A male patient about 65 years old · the chart notes a previous melanoma.
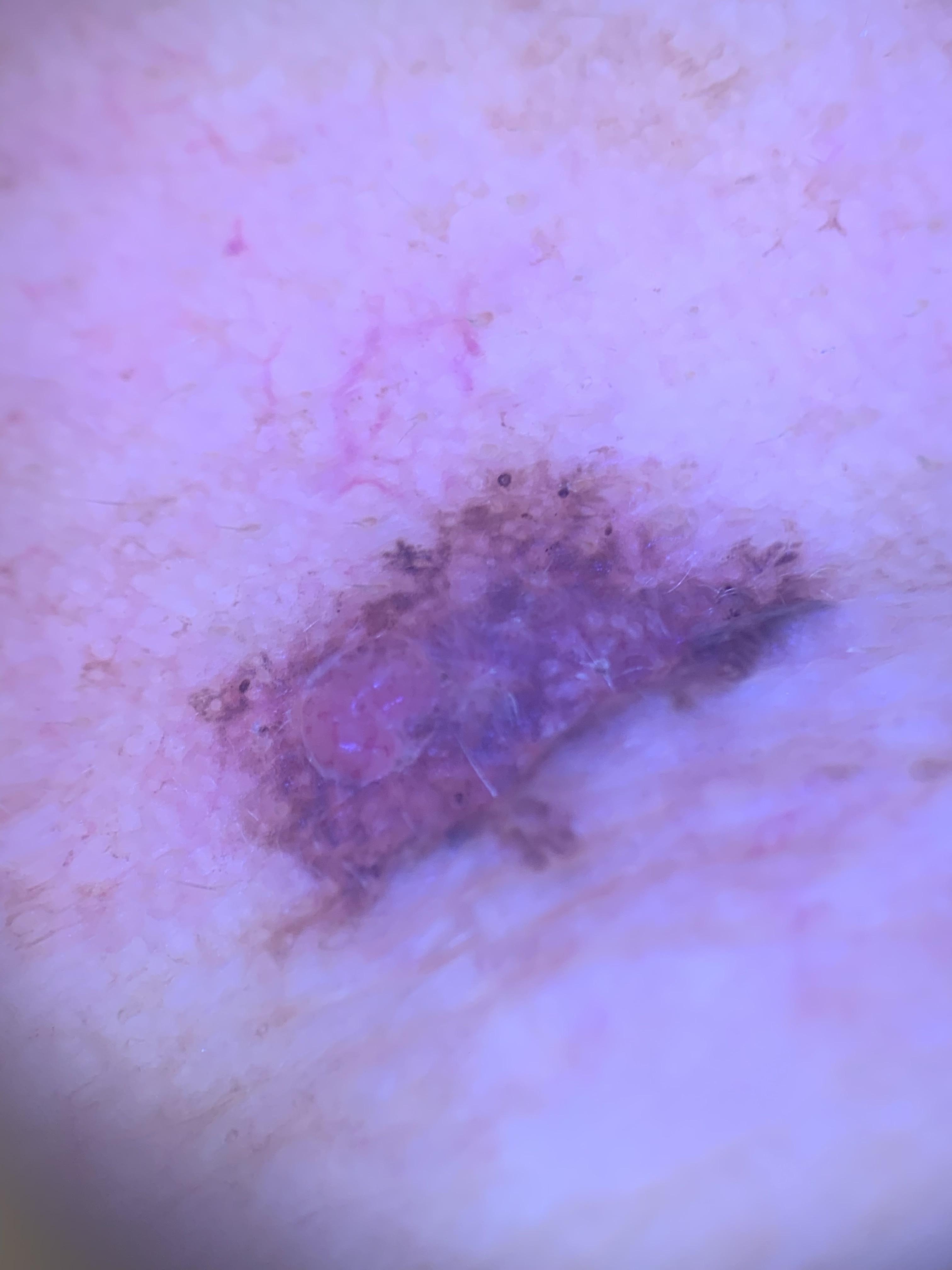location = the head or neck
diagnosis = Melanoma (biopsy-proven)